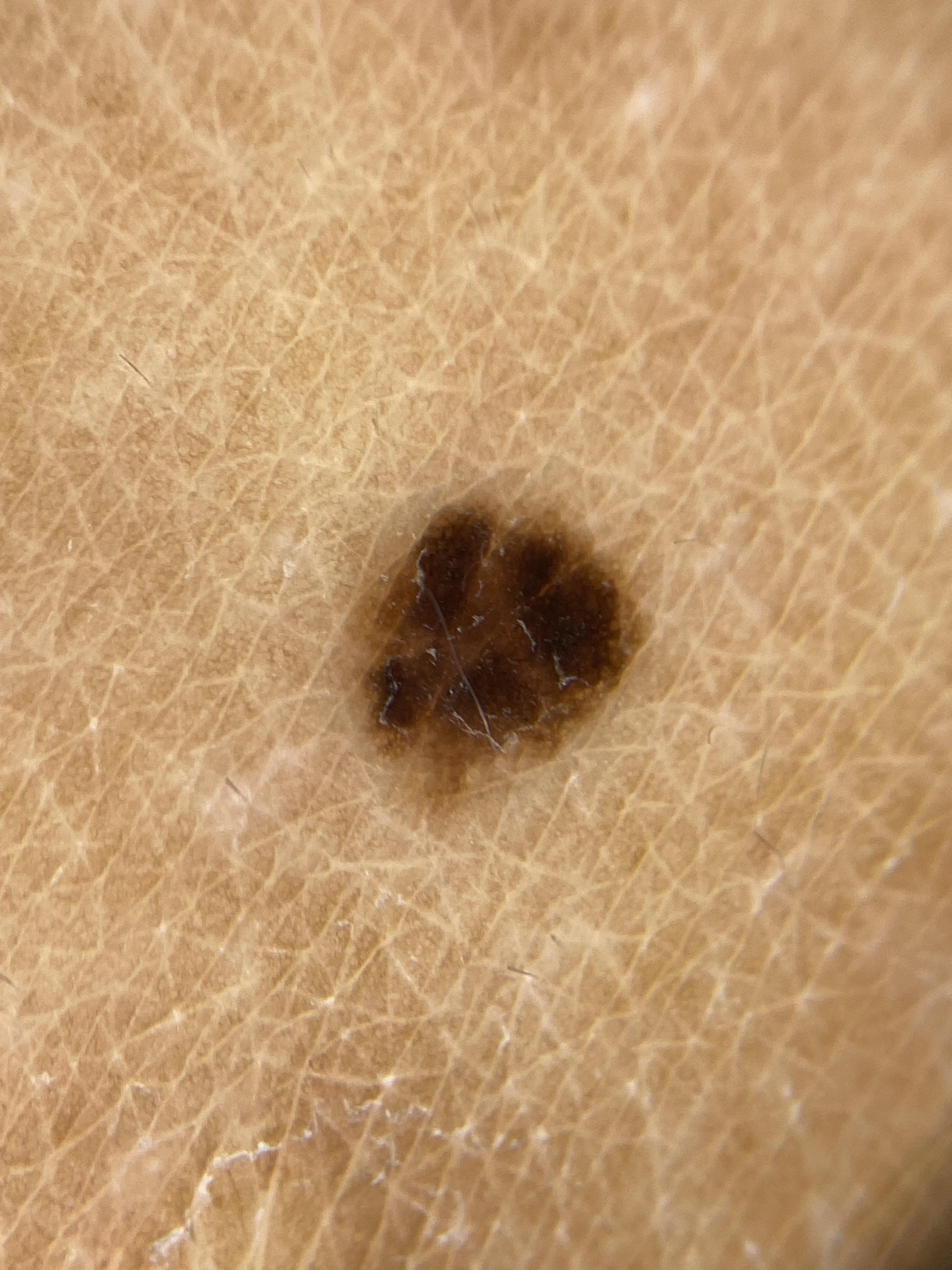Summary: Recorded as FST II. A female patient approximately 25 years of age. Located on a lower extremity. Conclusion: Histopathological examination showed a nevus.